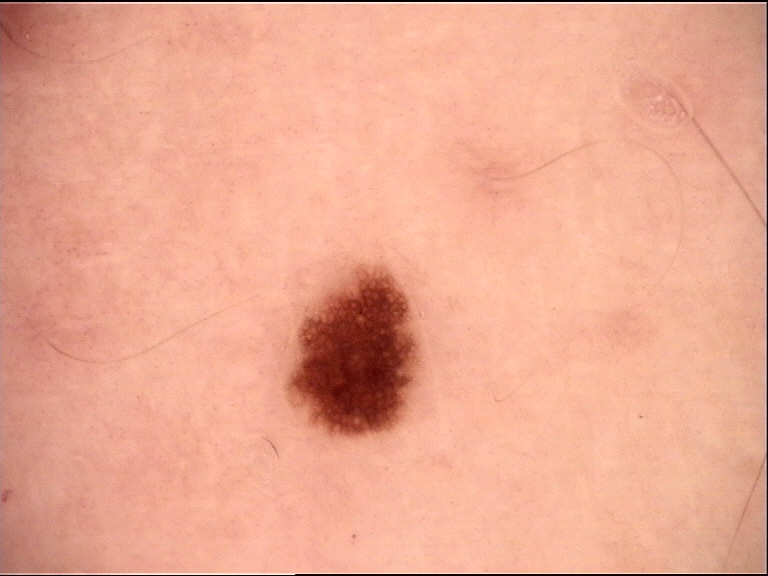<lesion>
  <image>dermatoscopy</image>
  <diagnosis>
    <name>dysplastic junctional nevus</name>
    <code>jd</code>
    <malignancy>benign</malignancy>
    <super_class>melanocytic</super_class>
    <confirmation>expert consensus</confirmation>
  </diagnosis>
</lesion>